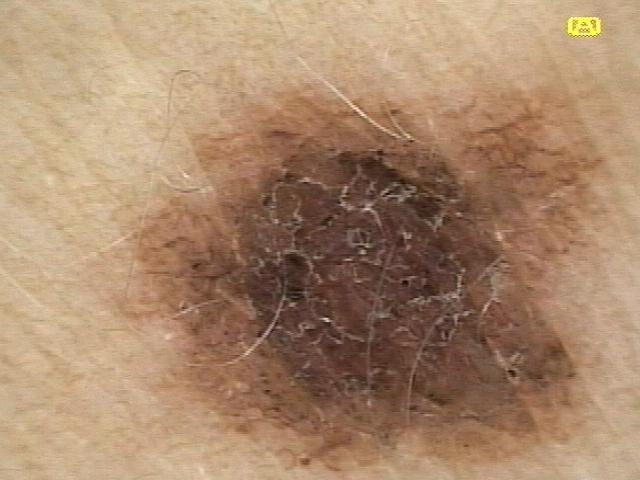A female patient roughly 20 years of age.
The lesion is on an upper extremity.
Expert review favored a nevus.